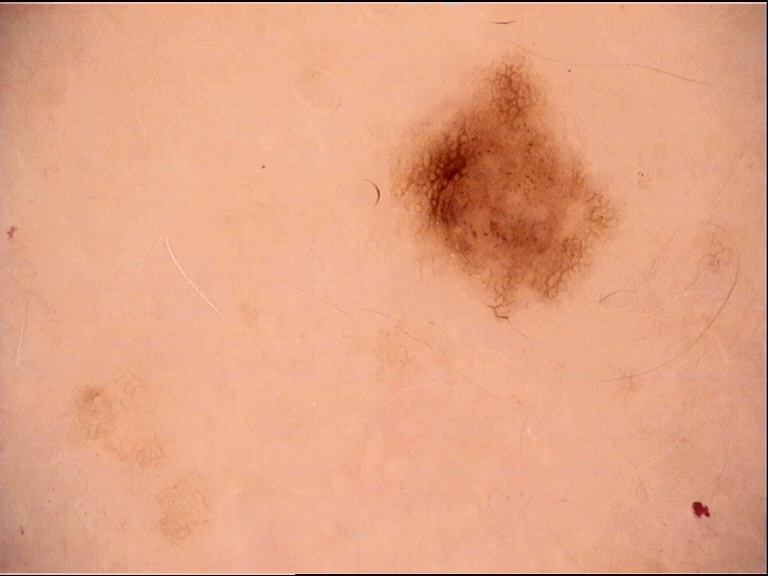assessment: dysplastic junctional nevus (expert consensus)